Acquired for a research image collection, with no referral diagnosis. Few moles overall by the patient's own estimate. A dermoscopic image of a skin lesion. A male patient 66 years old. The patient says their skin reddens with sun exposure. By self-report, a prior organ transplant:
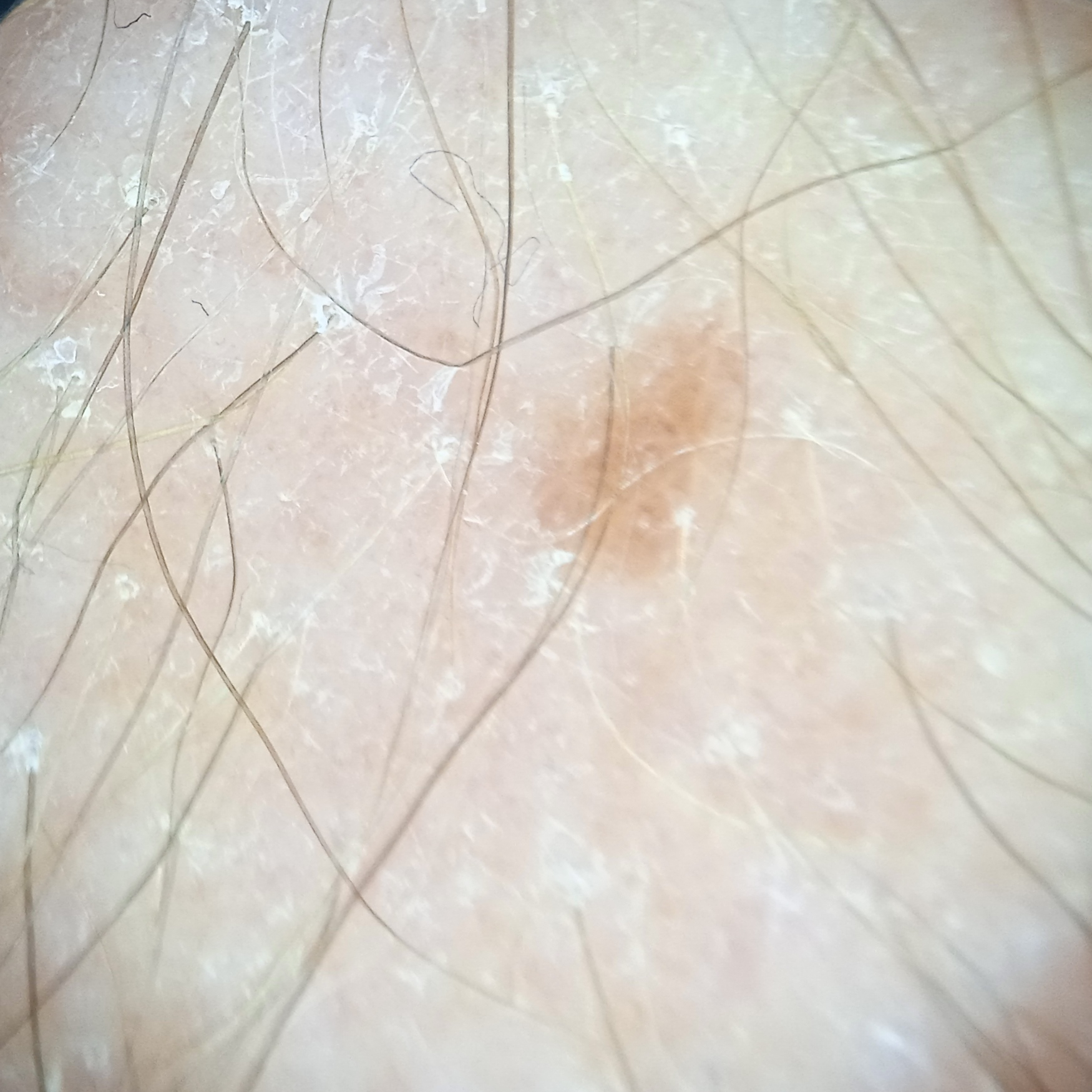Q: Where is the lesion?
A: an arm
Q: Lesion size?
A: 3.4 mm
Q: What was the diagnosis?
A: melanocytic nevus (dermatologist consensus)